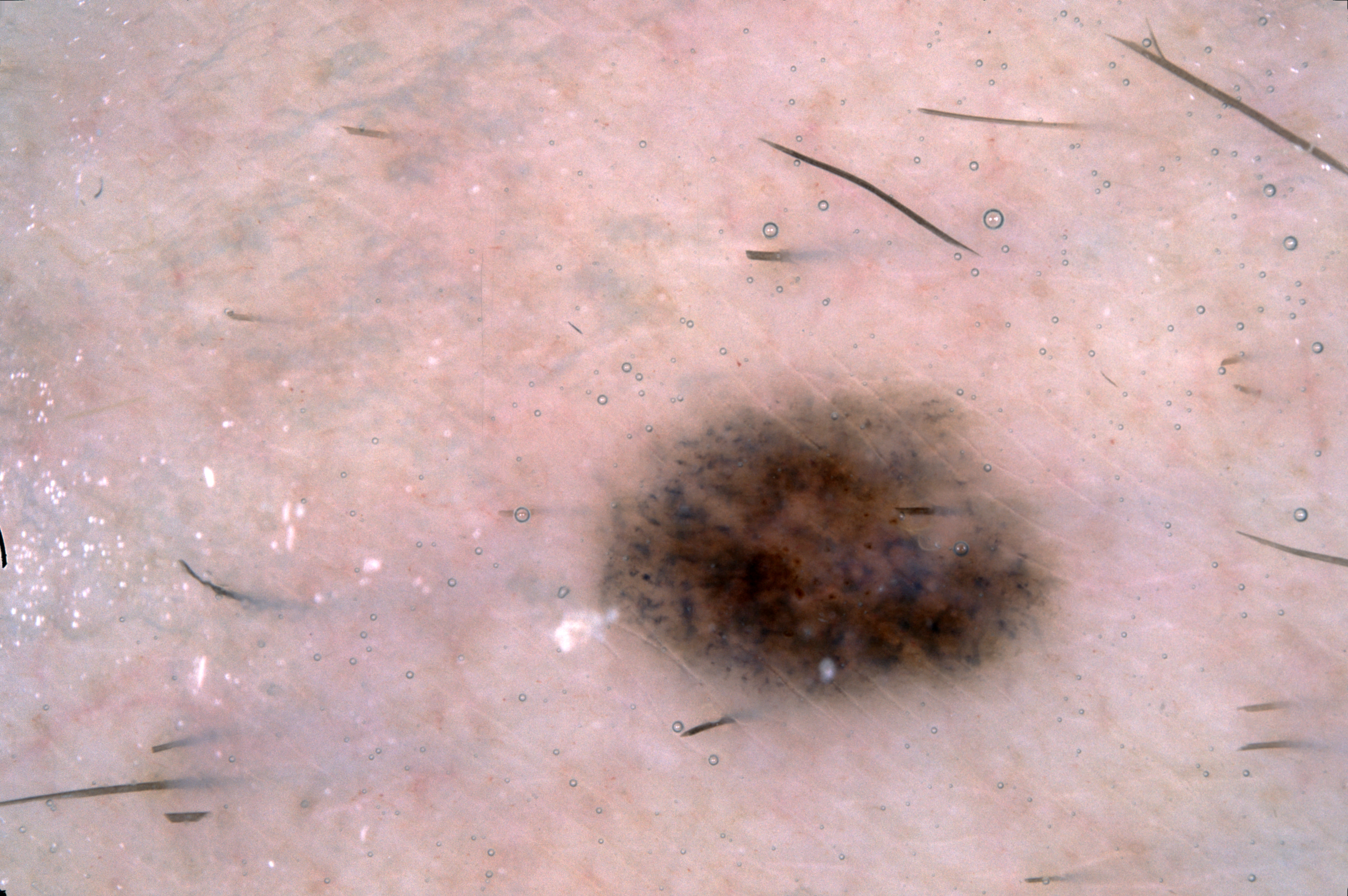Q: How was this image acquired?
A: dermatoscopic image of a skin lesion
Q: Patient demographics?
A: male, aged around 40
Q: What does dermoscopy show?
A: pigment network; absent: milia-like cysts, streaks, and negative network
Q: Where is the lesion in the image?
A: <box>601, 392, 1063, 707</box>
Q: What did the assessment conclude?
A: a melanocytic nevus